Located on the arm, head or neck, back of the hand, front of the torso and leg. The lesion is associated with enlargement, itching and bothersome appearance. An image taken at a distance. Texture is reported as raised or bumpy. The patient is a female aged 30–39.
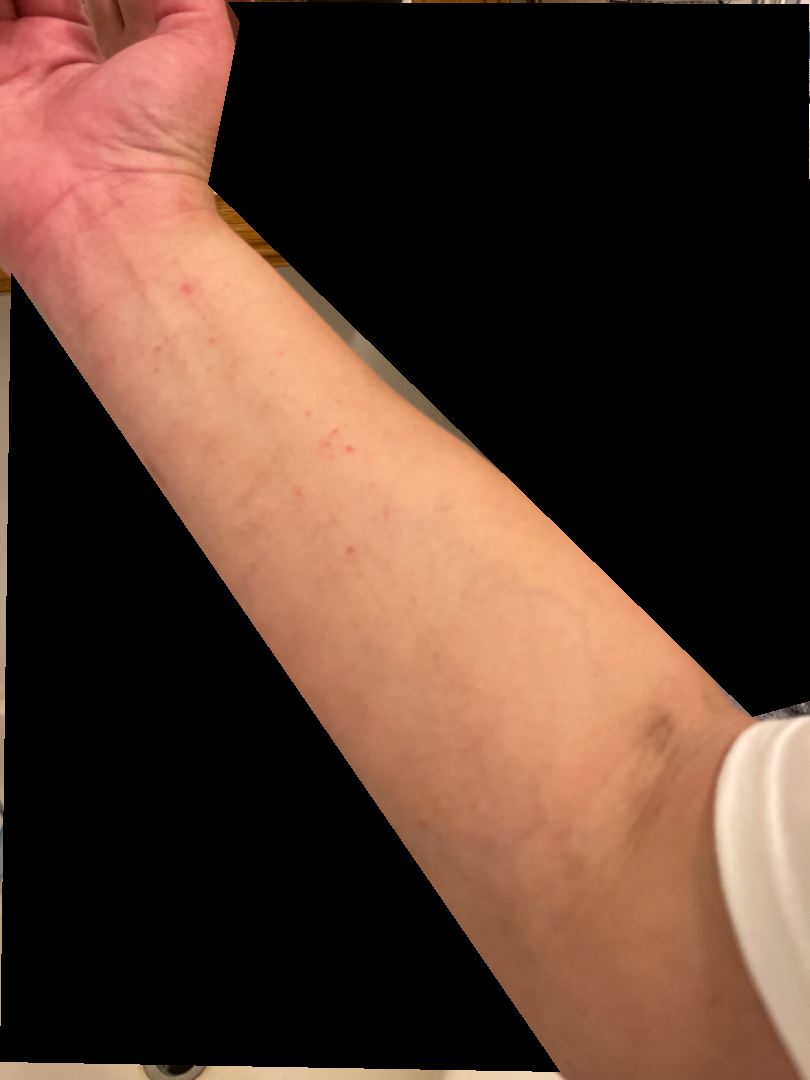The reviewer was unable to grade this case for skin condition.